A dermoscopic close-up of a skin lesion; a female patient roughly 65 years of age:
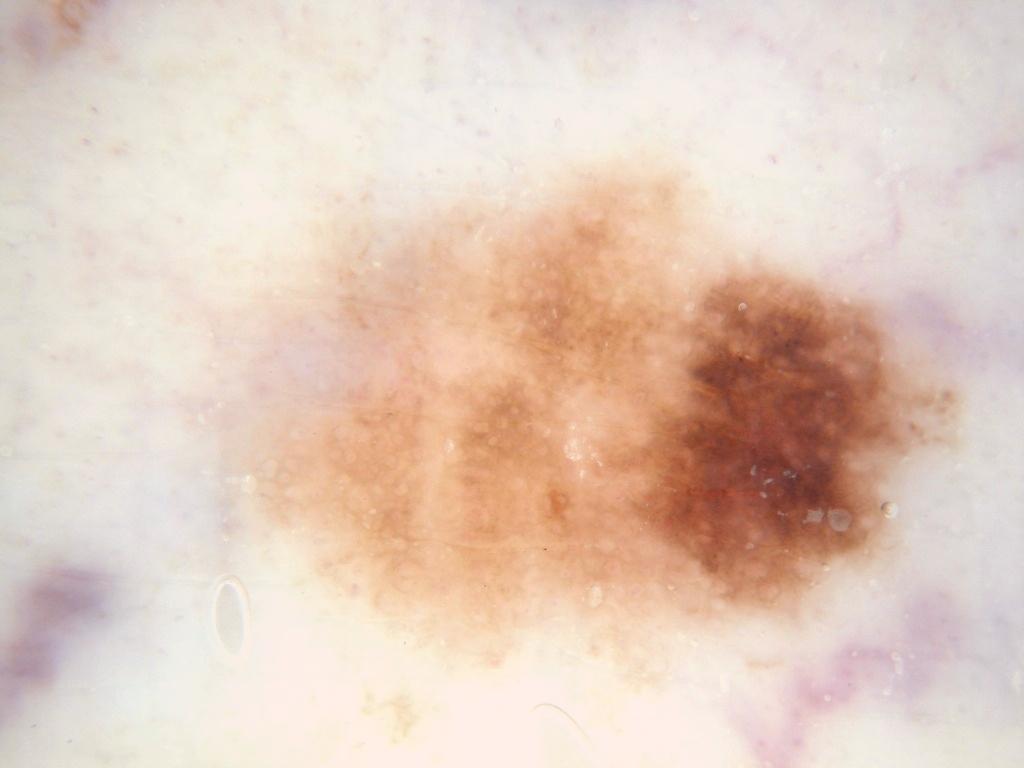As (left, top, right, bottom), lesion location: bbox(152, 146, 970, 714). Dermoscopic review identifies pigment network and globules, with no milia-like cysts, negative network, or streaks. The lesion was assessed as a melanocytic nevus.